A dermoscopic close-up of a skin lesion:
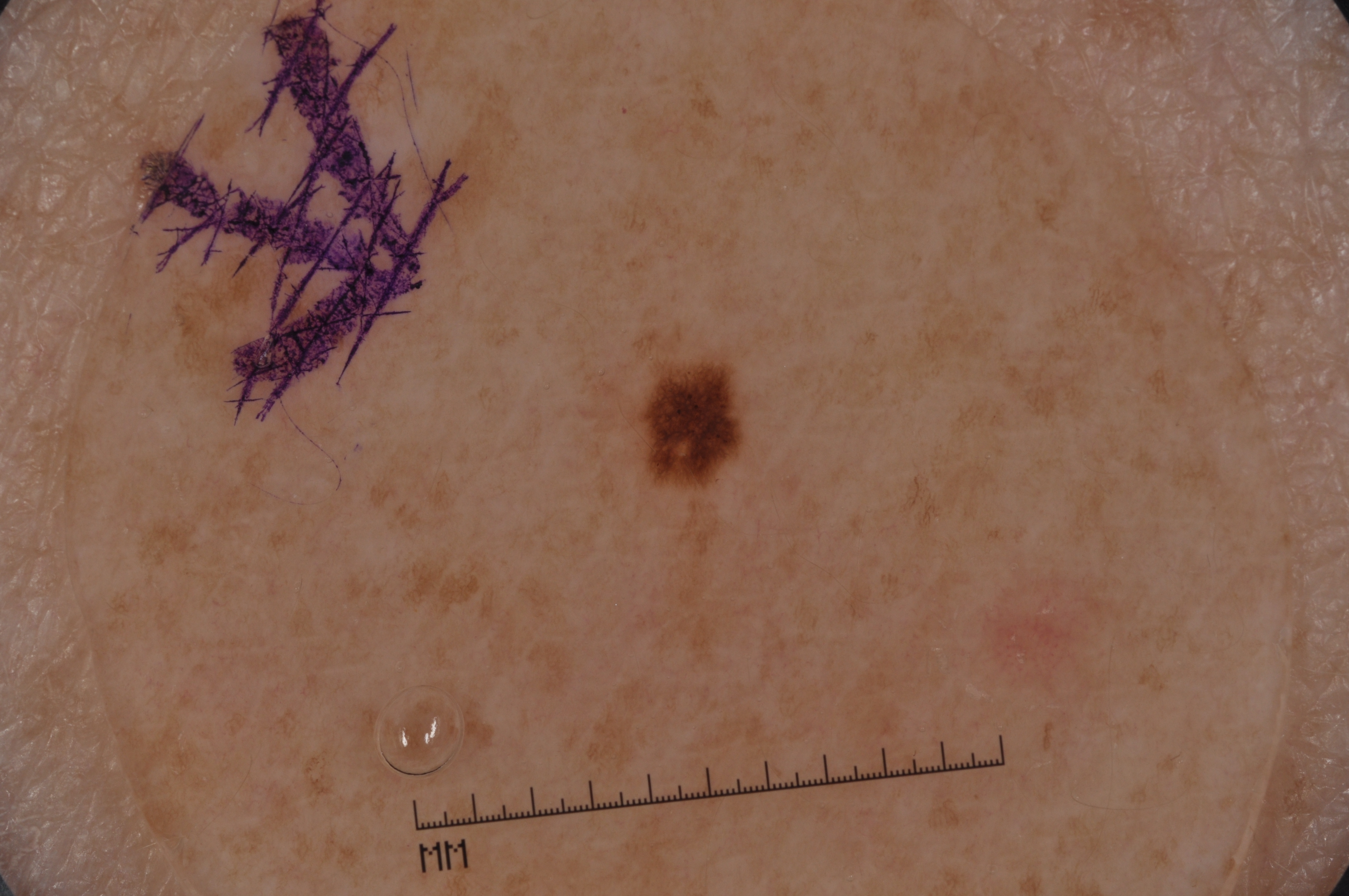With coordinates (x1, y1, x2, y2), the lesion occupies the region box(643, 365, 738, 476).
On dermoscopy, the lesion shows pigment network.
A small lesion within a wider field of skin.
Expert review diagnosed this as a melanocytic nevus, a benign skin lesion.